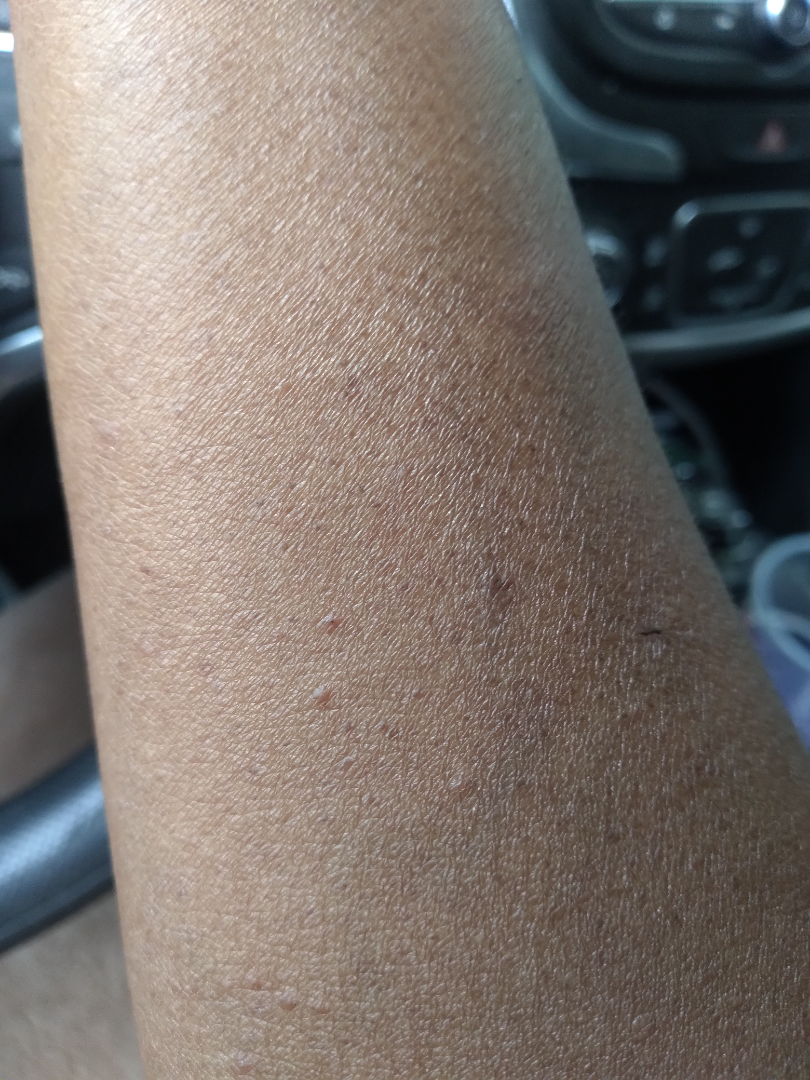| key | value |
|---|---|
| assessment | not assessable |
| anatomic site | head or neck |
| image framing | close-up |
| subject | female, age 60–69 |